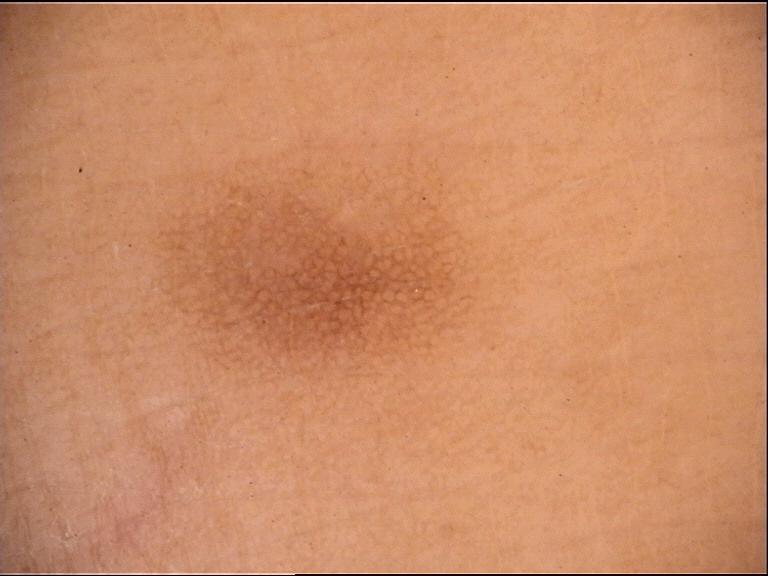imaging: dermatoscopy, subtype: fibro-histiocytic, assessment: dermatofibroma (expert consensus).